A dermoscopic image of a skin lesion · the patient was assessed as Fitzpatrick I · a female patient aged 68 to 72 · per the chart, a prior melanoma — 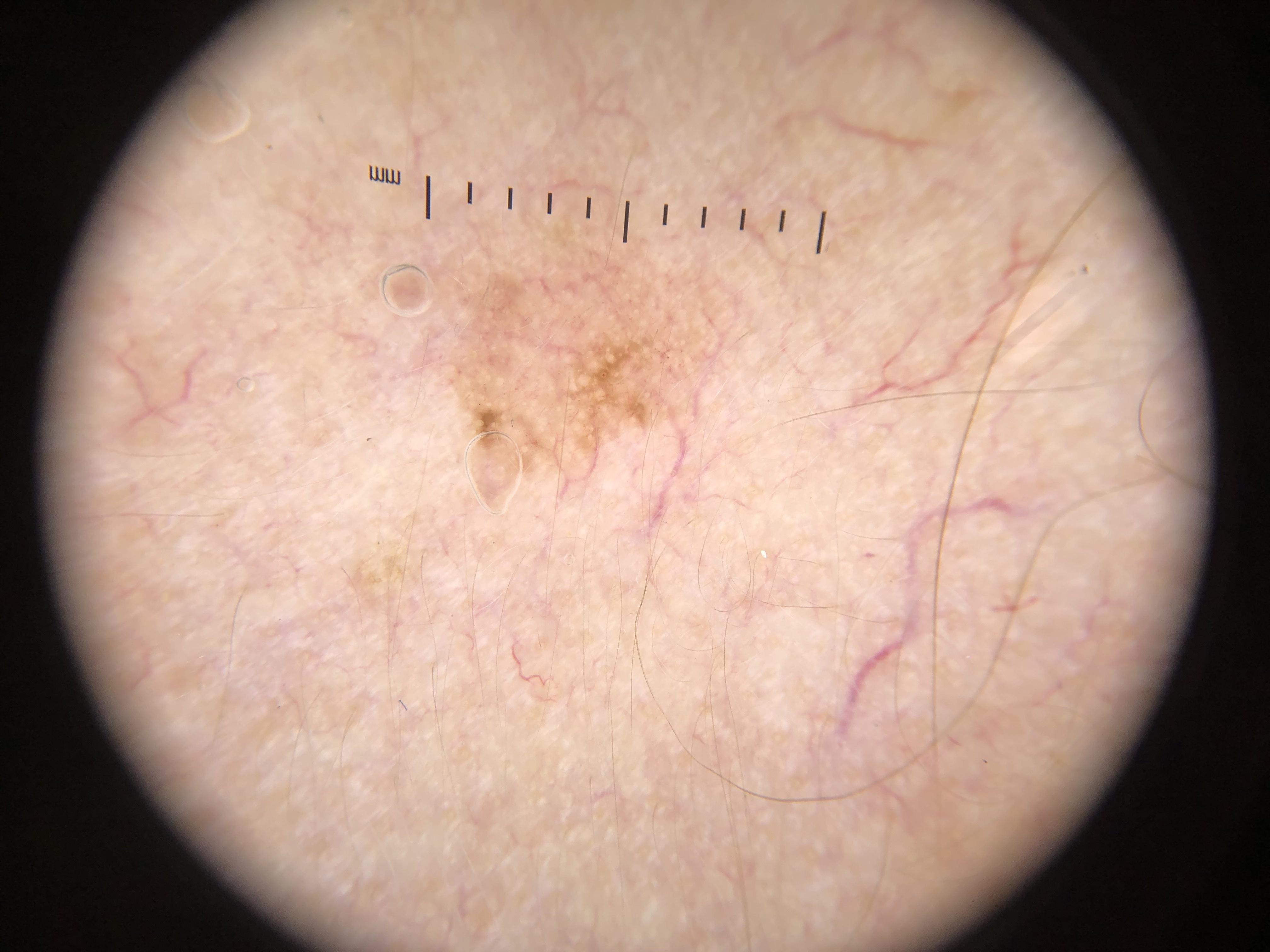Clinical context: The lesion is on the head or neck. Conclusion: The biopsy diagnosis was an epidermal proliferation — a seborrheic keratosis.